The patient did not report lesion symptoms. Female subject, age 18–29. No associated systemic symptoms reported. The leg is involved. Skin tone: non-clinician graders estimated Monk skin tone scale 1 or 2. The condition has been present for more than one year. Close-up view. Texture is reported as flat: 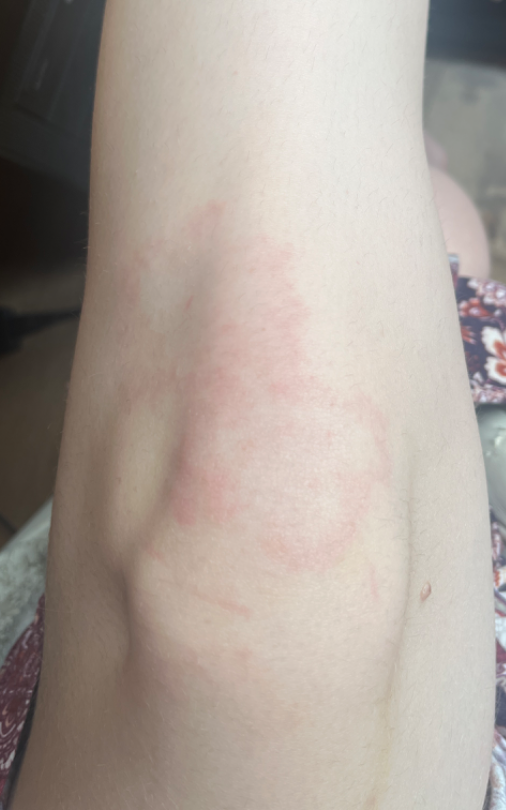On remote dermatologist review: Annular erythema (100%).